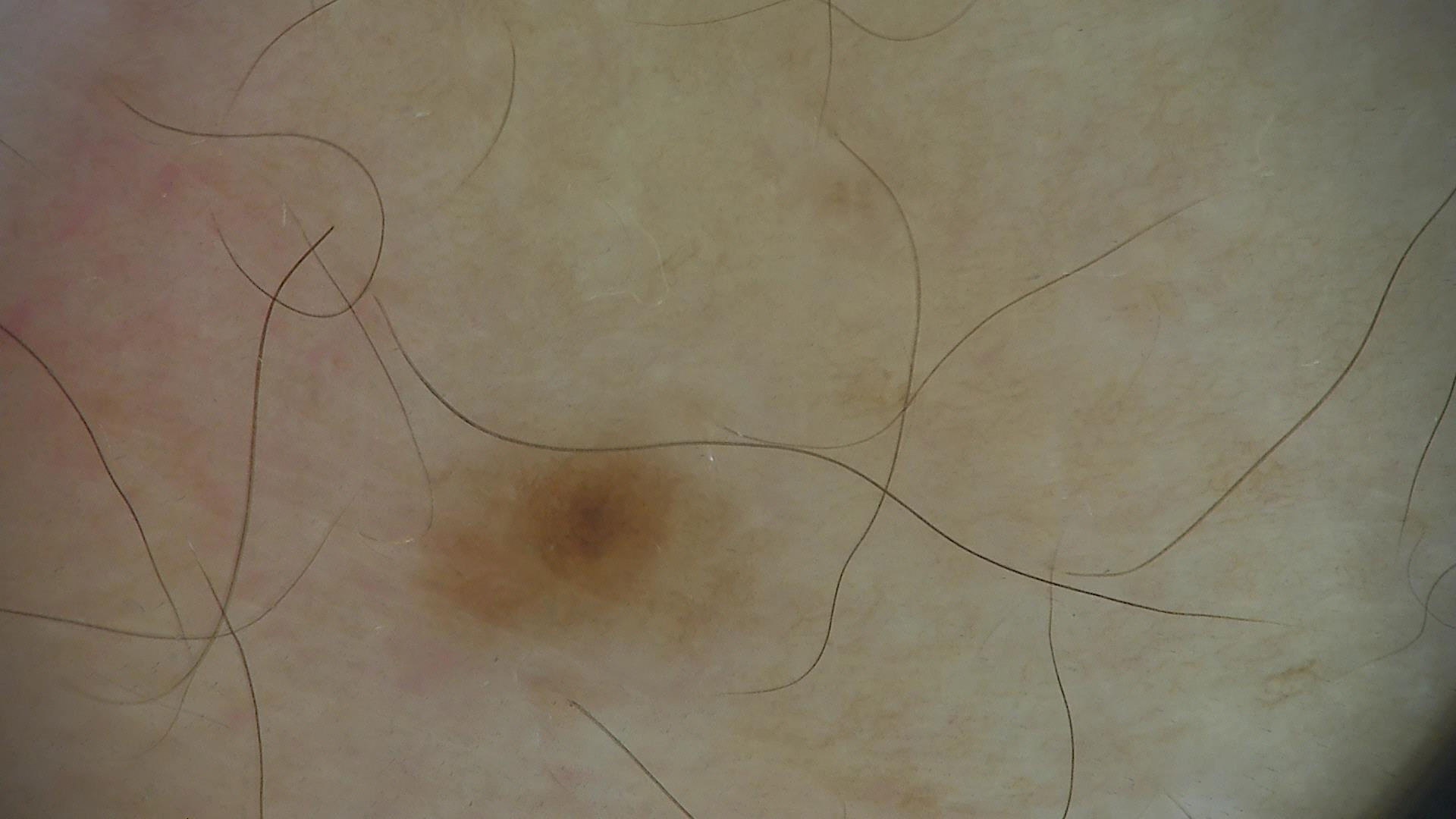Classified as a dysplastic junctional nevus.